A dermoscopic image of a skin lesion.
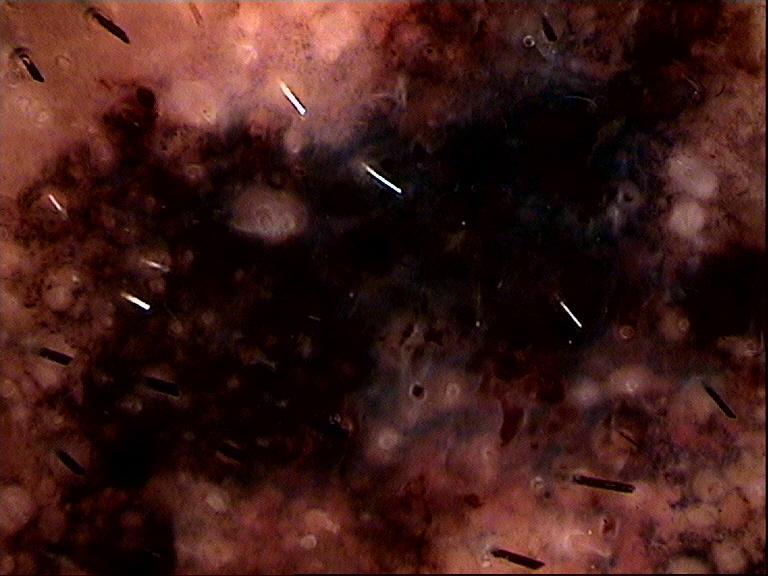Q: What is this lesion?
A: lentigo maligna melanoma (biopsy-proven)